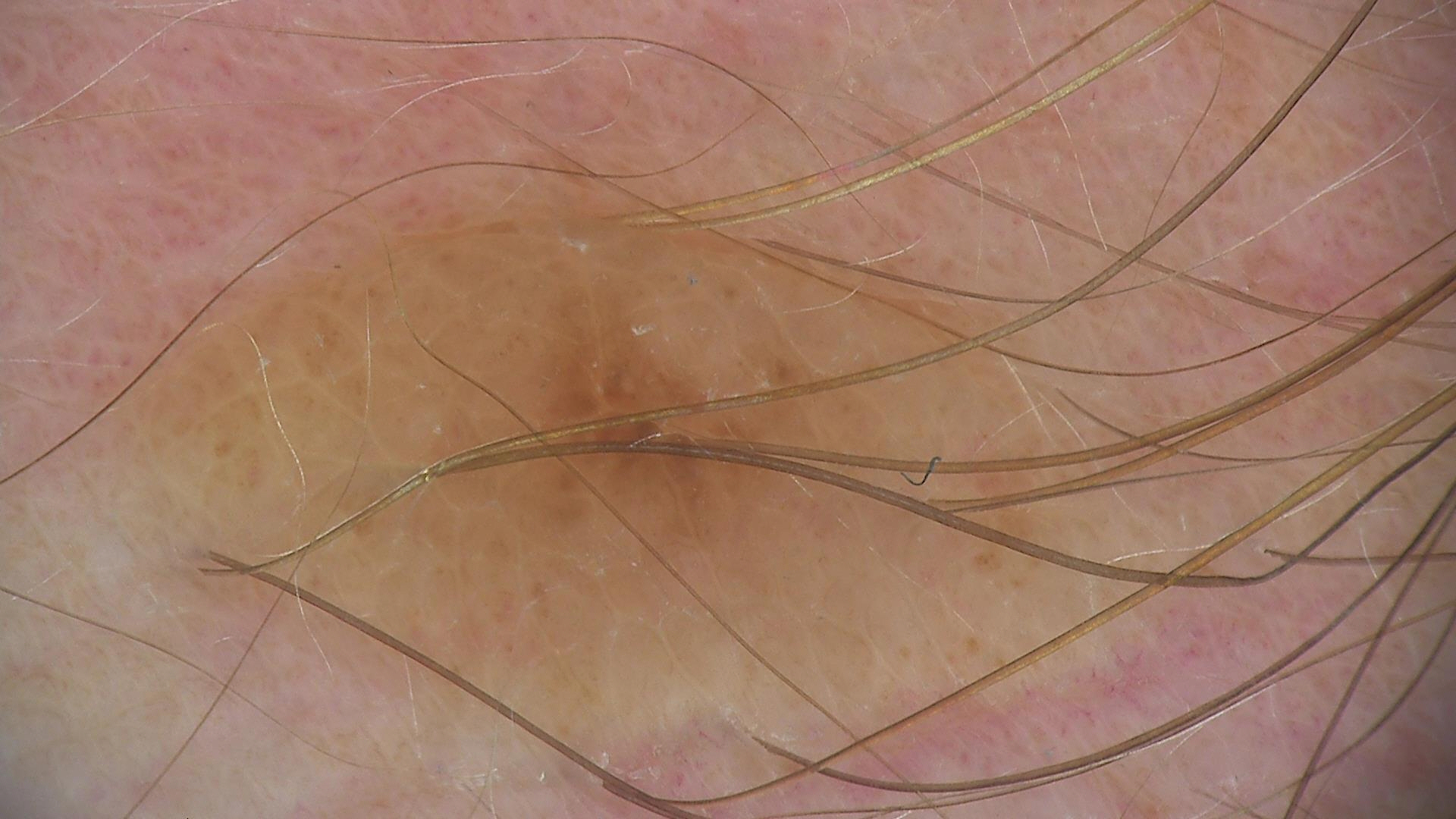assessment=dermal nevus (expert consensus).